A clinical photo of a skin lesion taken with a smartphone: 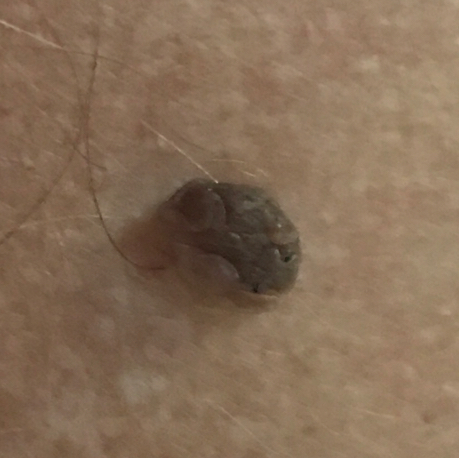| field | value |
|---|---|
| body site | the back |
| patient-reported symptoms | growth, elevation |
| diagnosis | nevus (clinical consensus) |